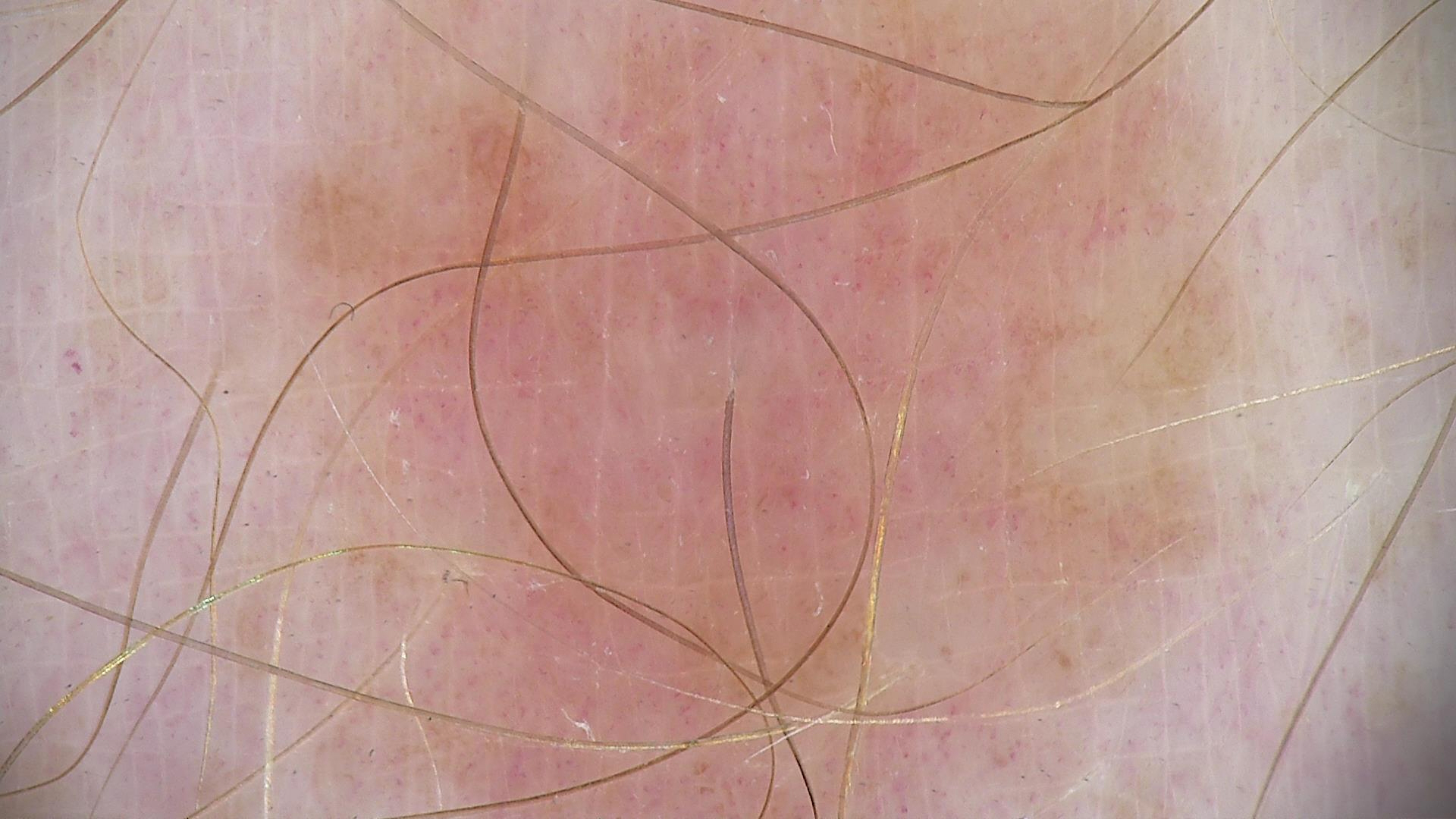The diagnostic label was a dysplastic junctional nevus.